A dermoscopy image of a single skin lesion.
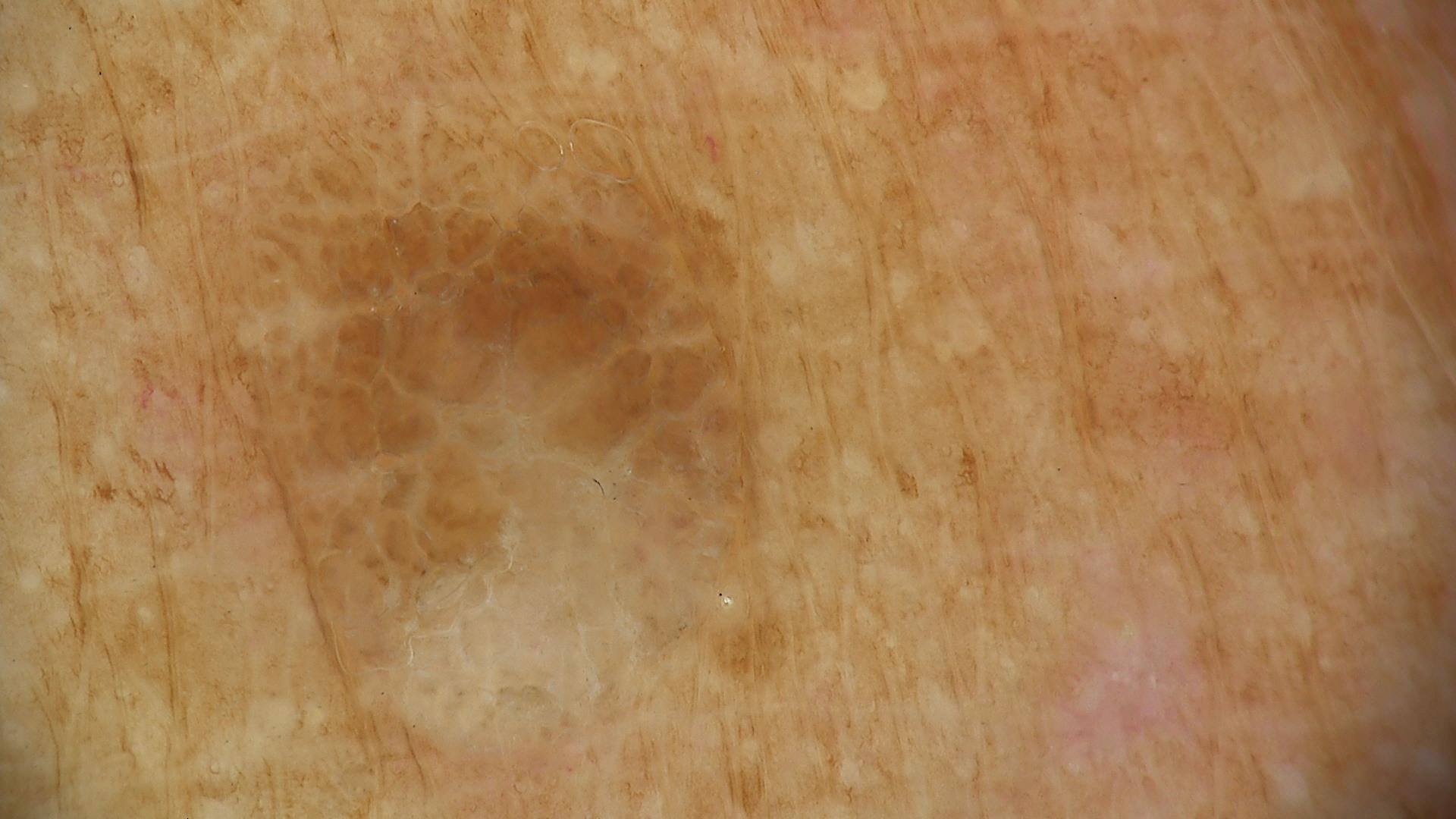Summary:
The architecture is that of a keratinocytic lesion.
Conclusion:
Diagnosed as a seborrheic keratosis.